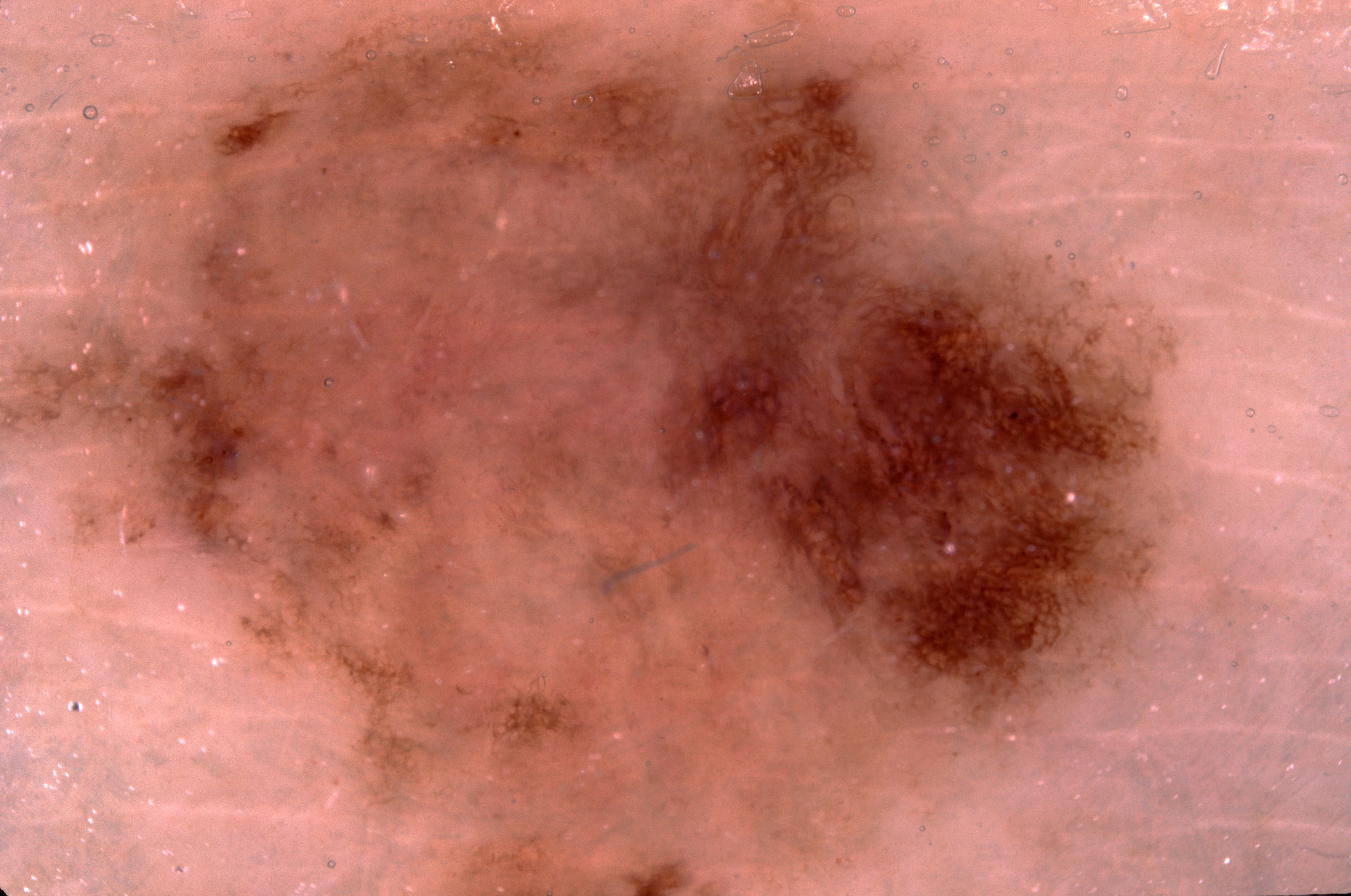A skin lesion imaged with a dermatoscope.
A female subject, in their 50s.
The dermoscopic pattern shows pigment network; no milia-like cysts, negative network, or streaks.
As (left, top, right, bottom), the lesion occupies the region [0, 0, 1194, 895].
The diagnostic assessment was a melanocytic nevus, a benign skin lesion.